This image was taken at an angle, the subject is female, located on the arm — 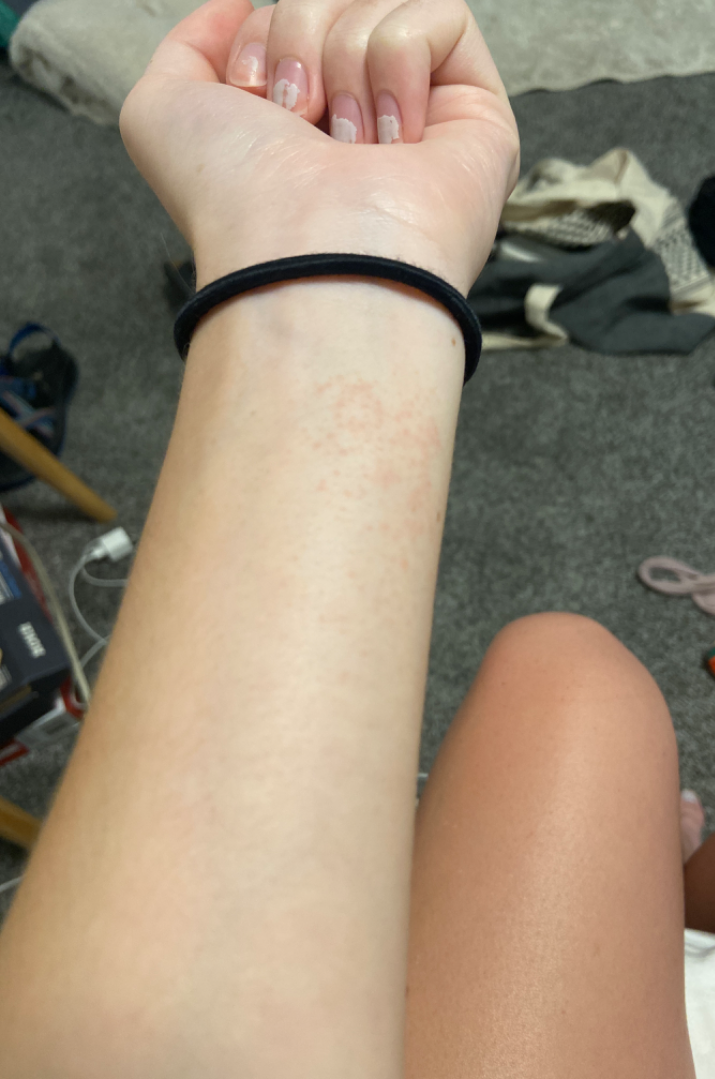<case>
<assessment>could not be assessed</assessment>
</case>